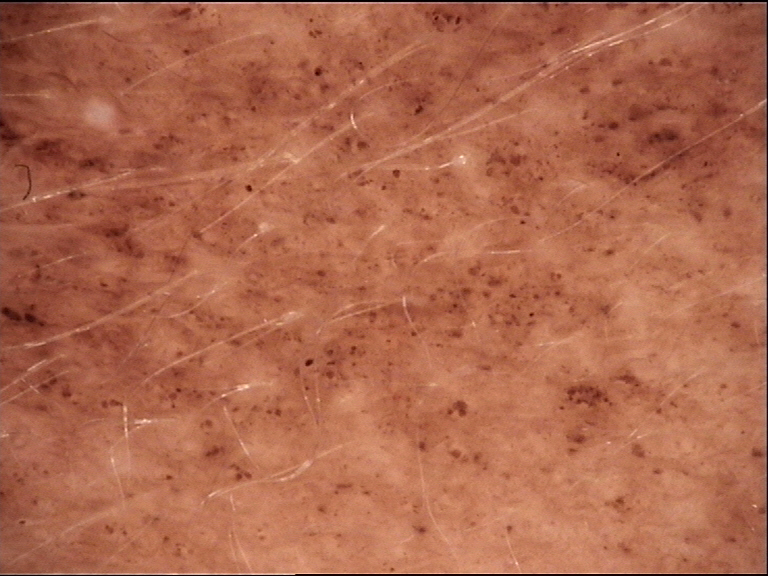Dermoscopy of a skin lesion. This is a banal lesion. The diagnostic label was a congenital junctional nevus.